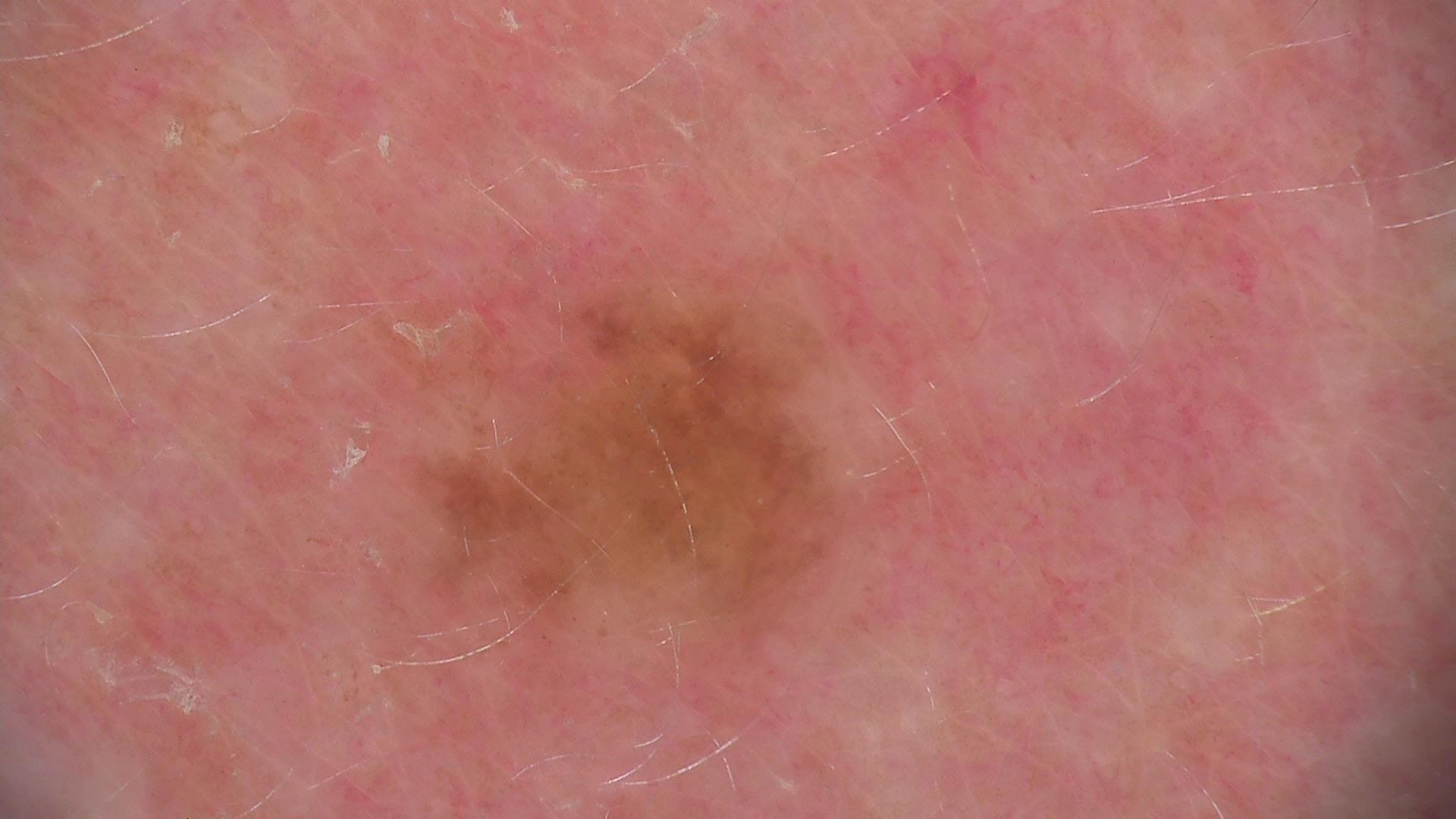imaging = dermoscopy, diagnostic label = dysplastic junctional nevus (expert consensus).